A male patient aged 73 to 77; a dermoscopic image of a skin lesion: 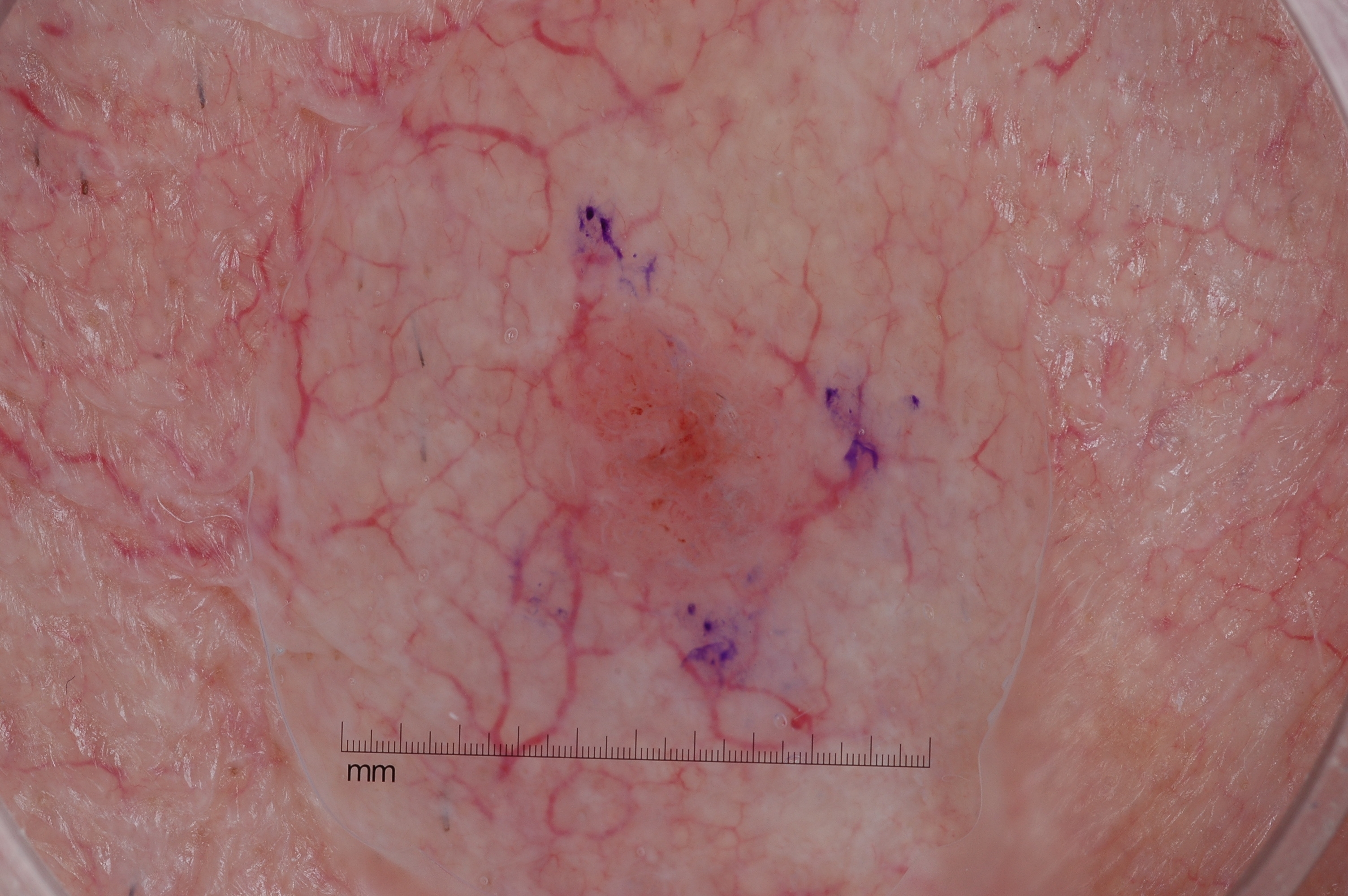With coordinates (x1, y1, x2, y2), the lesion occupies the region <box>506, 305, 832, 600</box>. The lesion occupies roughly 6% of the field. The dermoscopic pattern shows no negative network, streaks, milia-like cysts, or pigment network. The clinical diagnosis was a seborrheic keratosis.